A female subject roughly 50 years of age; a dermoscopy image of a single skin lesion.
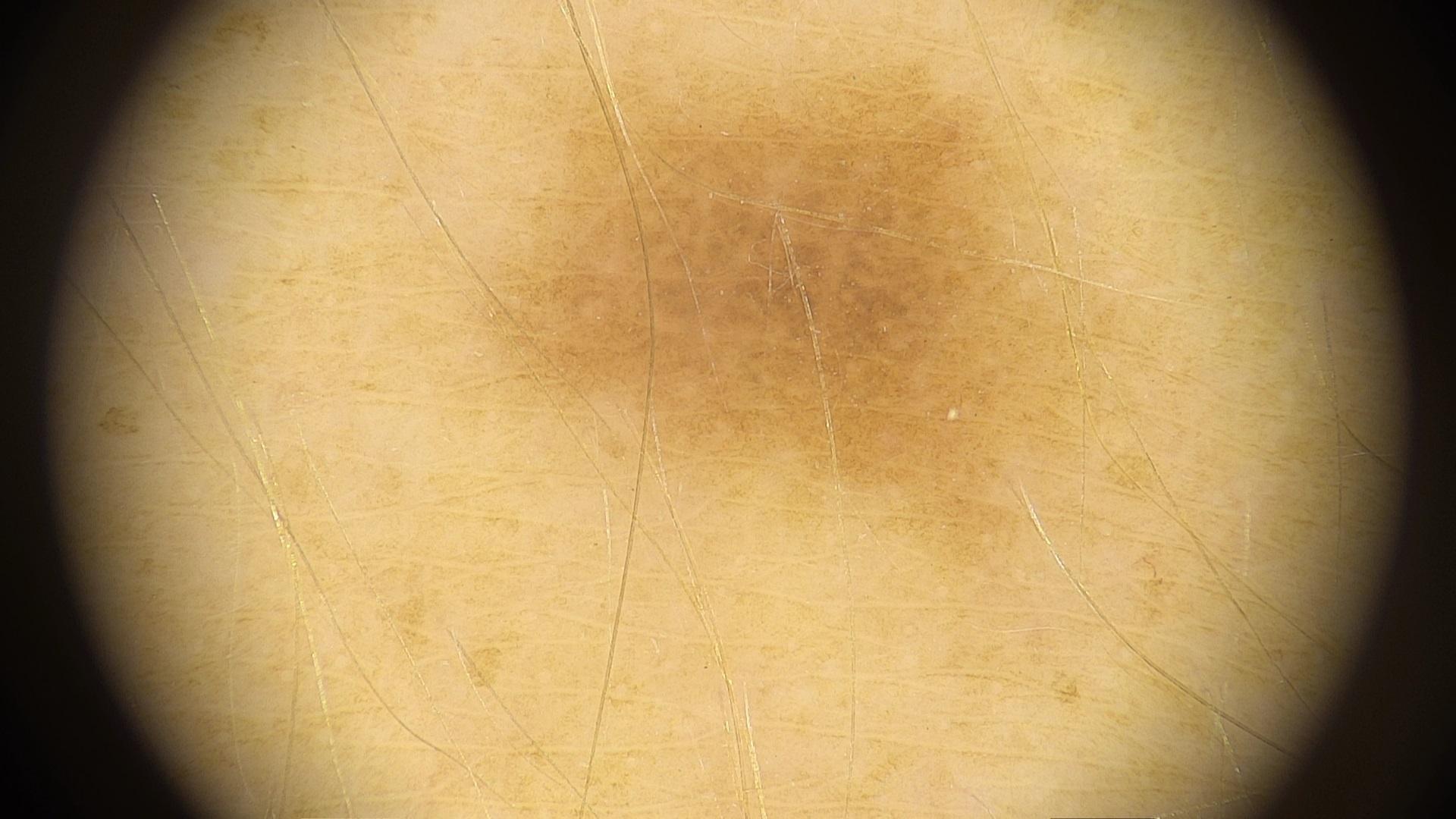Image and clinical context: The lesion involves an upper extremity. Assessment: Clinically diagnosed as a nevus.